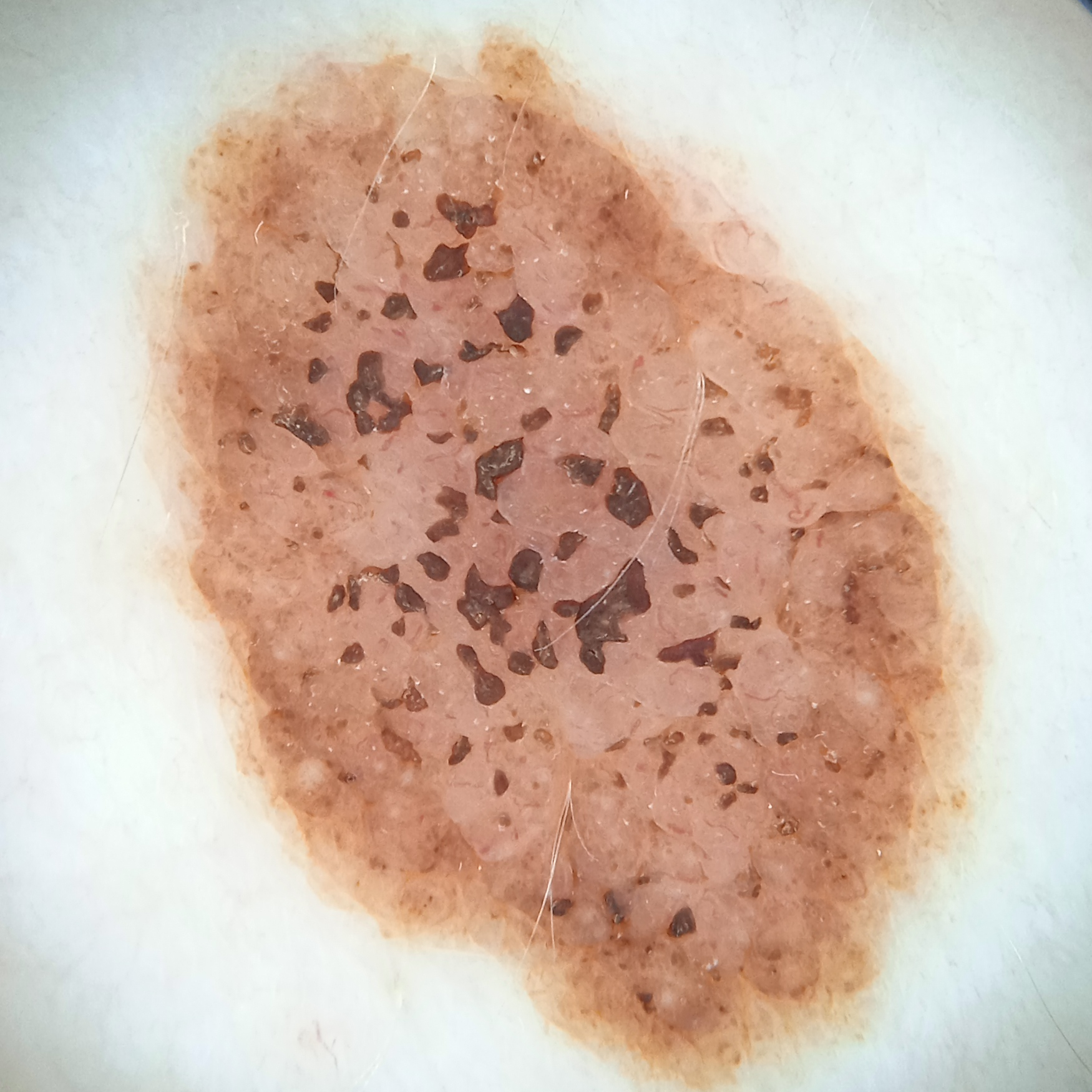A dermoscopic image of a skin lesion. On a questionnaire the patient reported a history of sunbed use, no immunosuppression, and no prior organ transplant. Acquired for a research image collection, with no referral diagnosis. Numerous moles by the patient's own estimate. A female patient age 26. The patient says their skin reddens with sun exposure. Located on the torso. The lesion is about 12.1 mm across. Dermatologist review favored a melanocytic nevus.